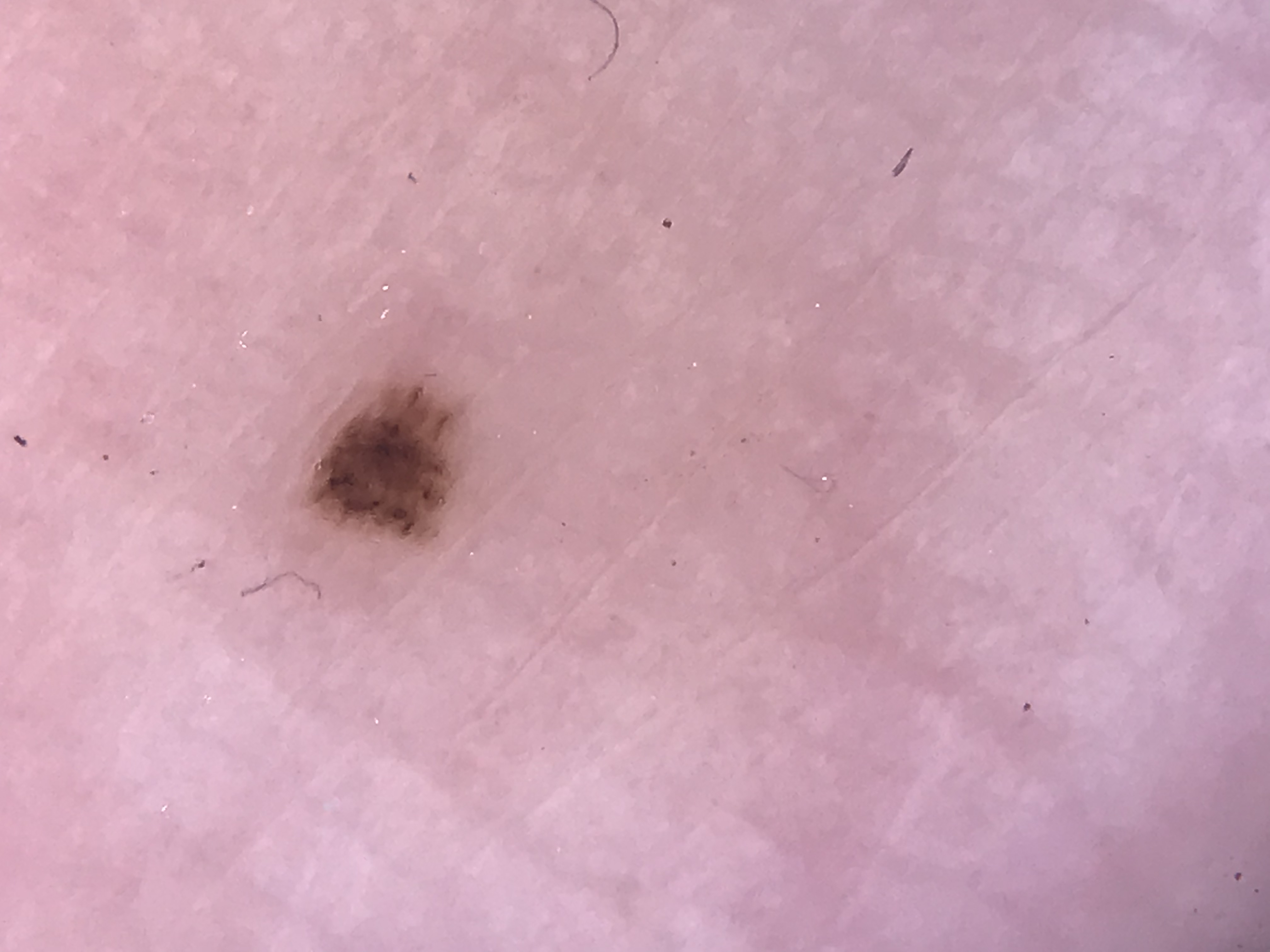Diagnosed as an acral dysplastic junctional nevus.